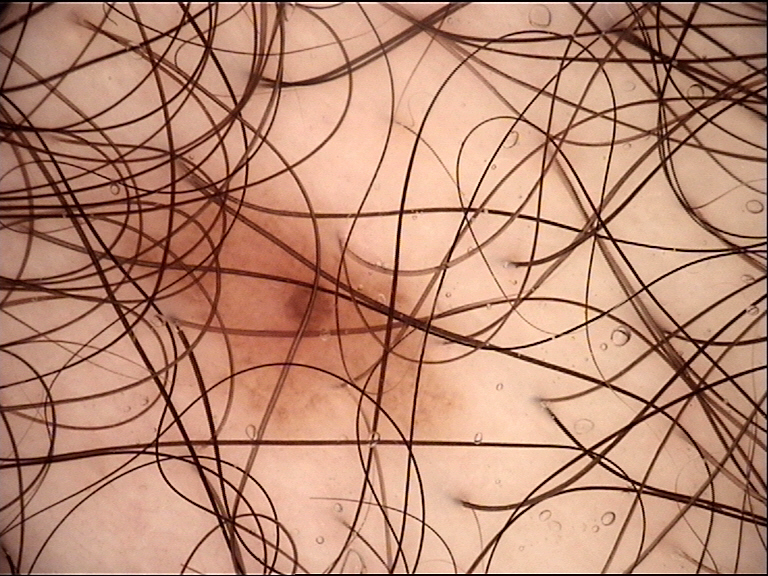image=dermatoscopy
label=dysplastic junctional nevus (expert consensus)